A close-up photograph. Located on the arm.
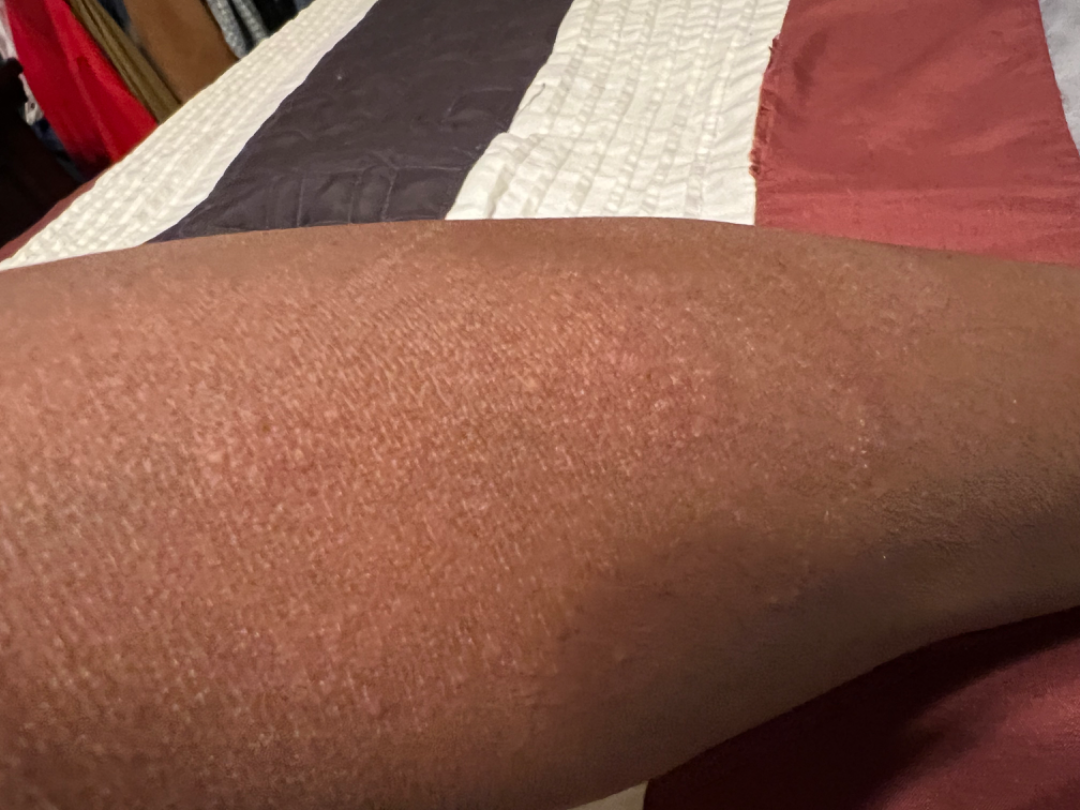  assessment: indeterminate from the photograph